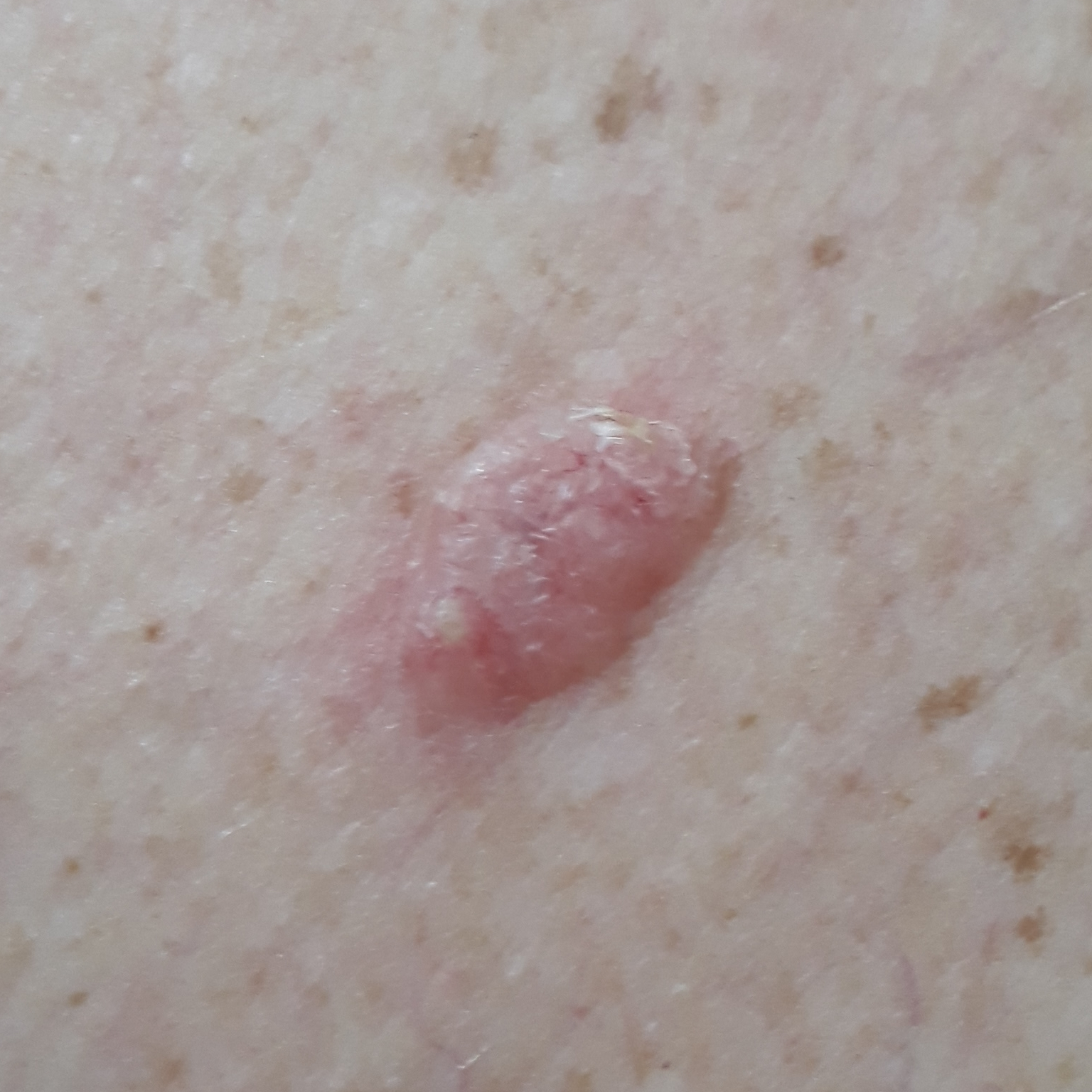Biopsy-confirmed as a basal cell carcinoma.